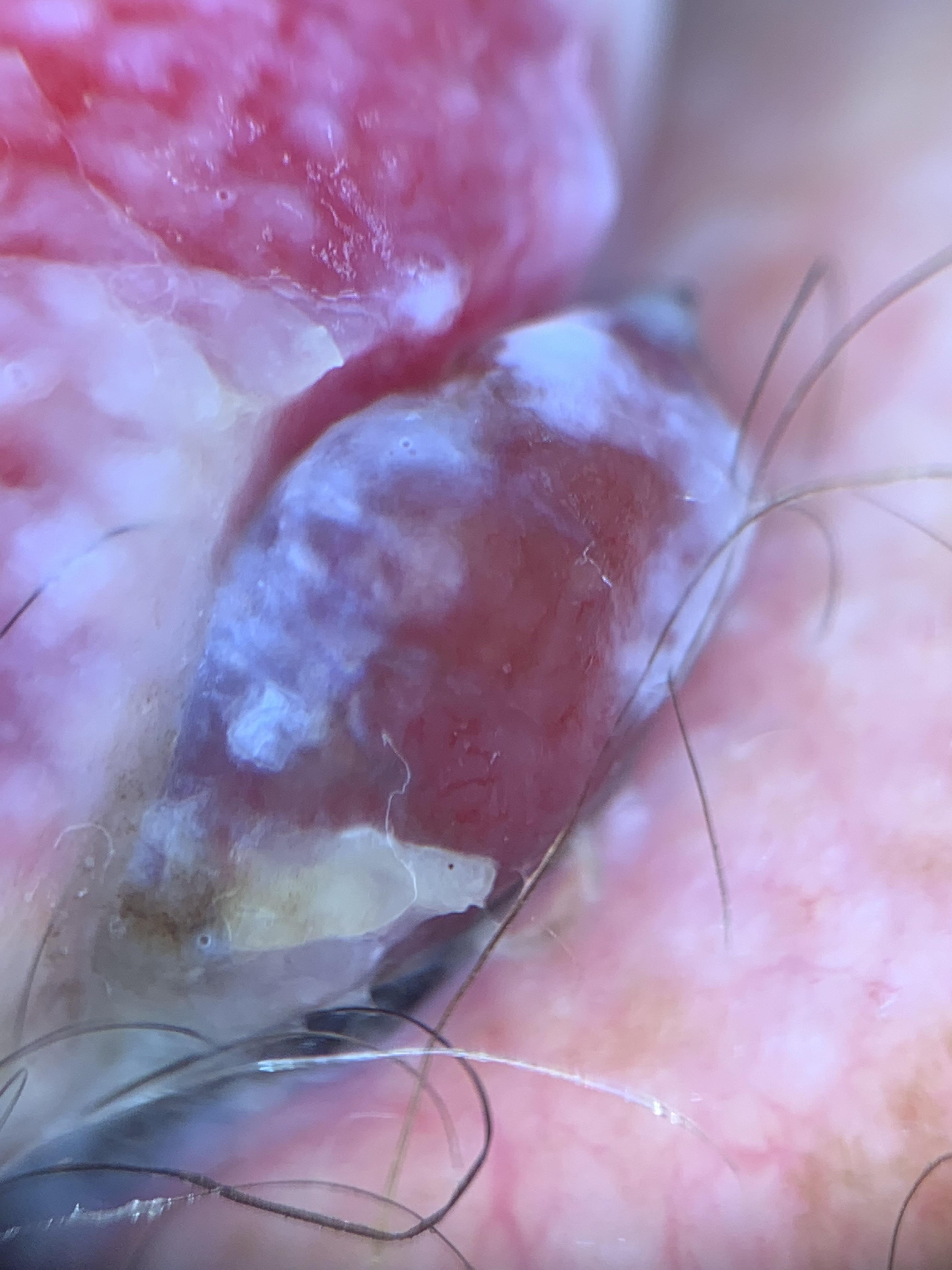Contact-polarized dermoscopy of a skin lesion. A male subject in their mid-80s or older. The lesion is on an upper extremity. Histopathology confirmed a melanoma.